A close-up photograph. The head or neck is involved: 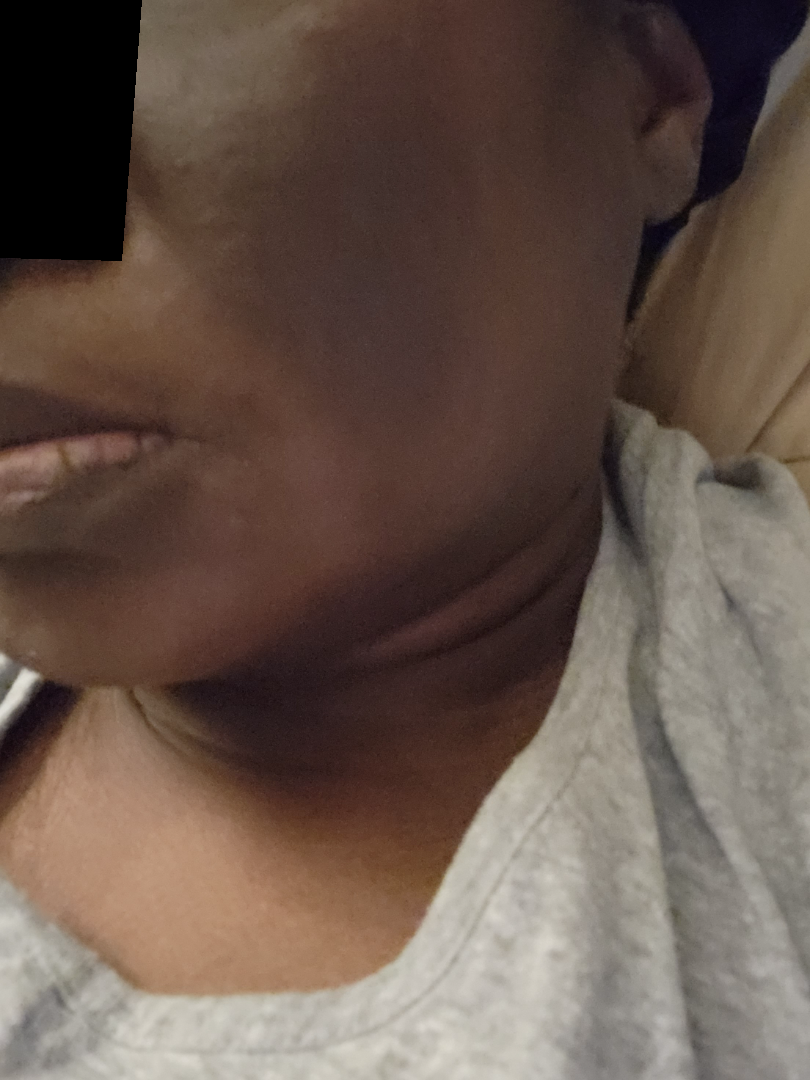Self-categorized by the patient as a pigmentary problem.
Present for more than one year.
Associated systemic symptoms include fatigue and joint pain.
Fitzpatrick skin type V.
The primary impression is Post-Inflammatory hyperpigmentation; possibly Melasma; also on the differential is Drug induced abnormal pigmentation of skin.